A dermoscopic close-up of a skin lesion: 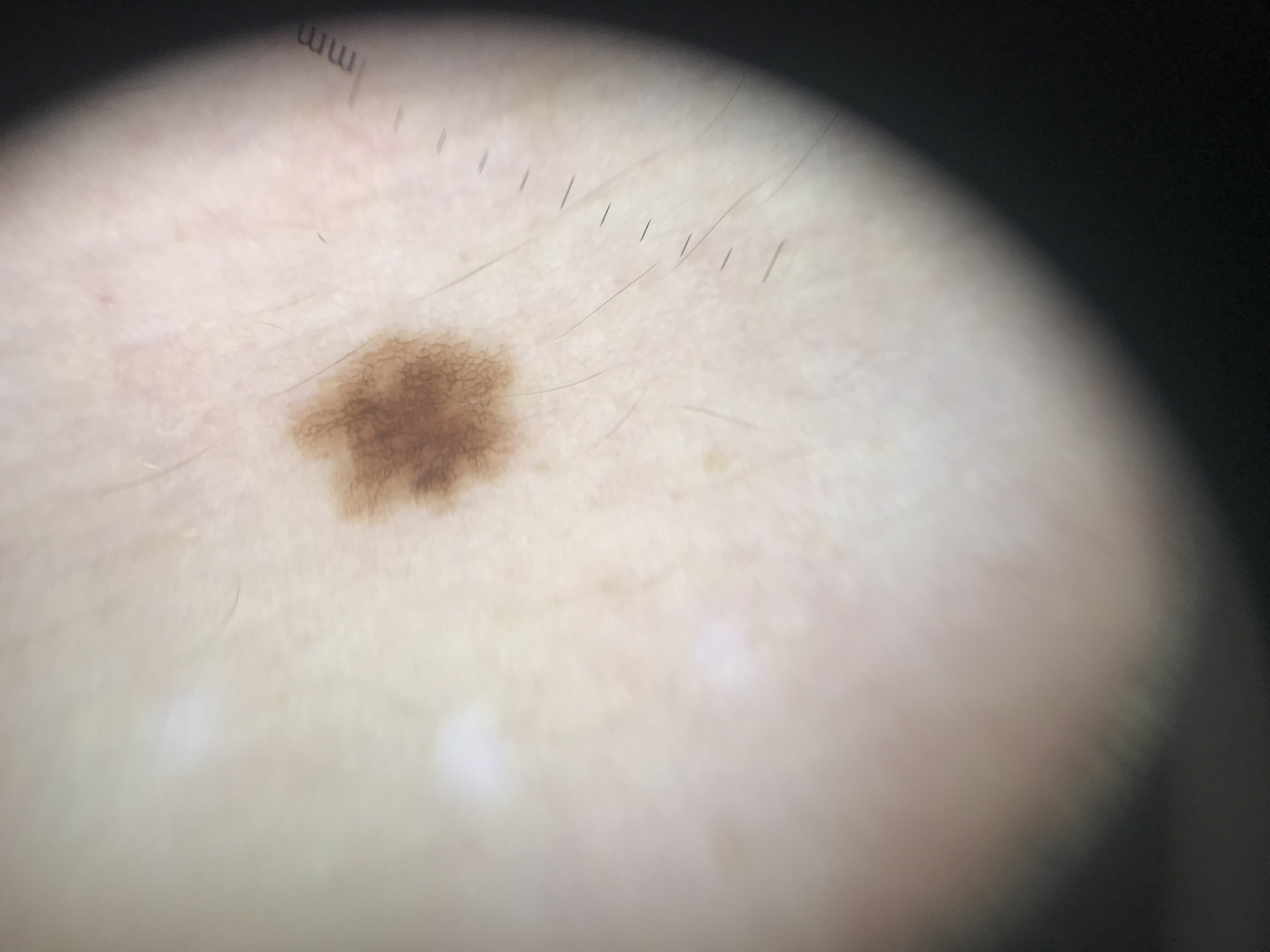Q: What was the diagnostic impression?
A: dysplastic junctional nevus (expert consensus)